The affected area is the leg. The patient described the issue as a growth or mole. Reported lesion symptoms include pain, darkening, bleeding, enlargement, bothersome appearance, itching and burning. The contributor reports the lesion is rough or flaky, raised or bumpy, fluid-filled and flat. A close-up photograph. The patient also reports joint pain, fatigue, chills, fever and mouth sores. Fitzpatrick skin type III; human graders estimated Monk Skin Tone 1–2. Present for more than one year:
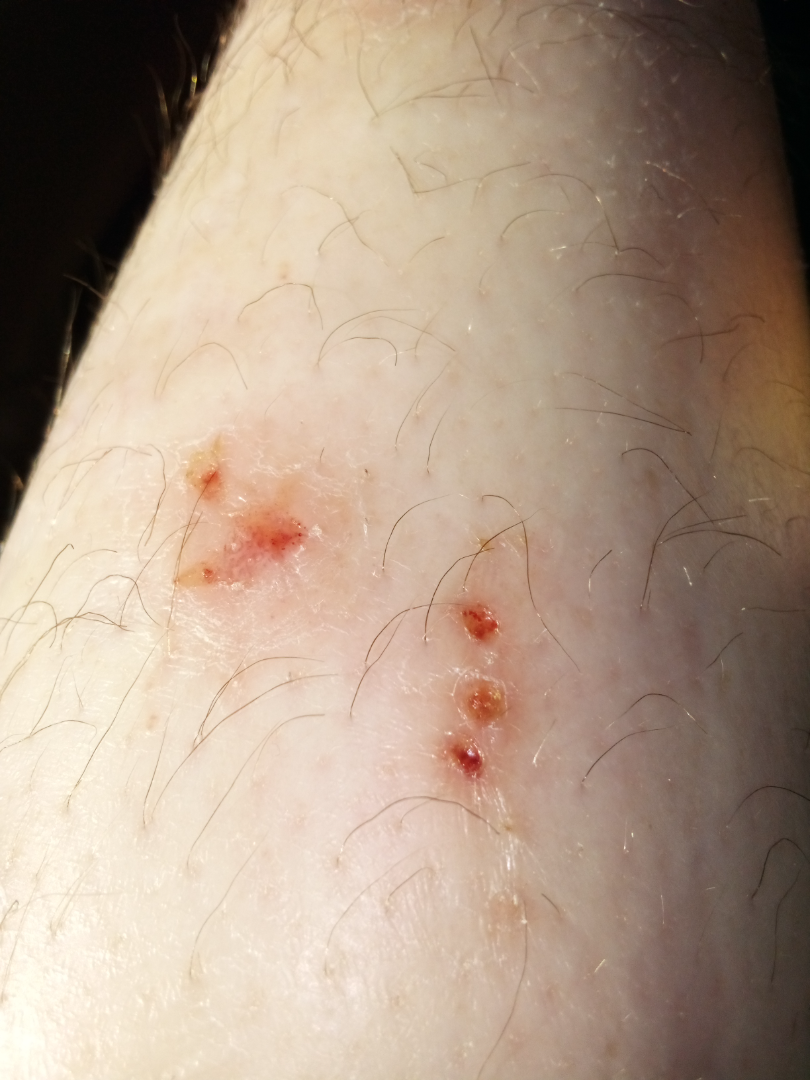Notes:
– assessment: unable to determine